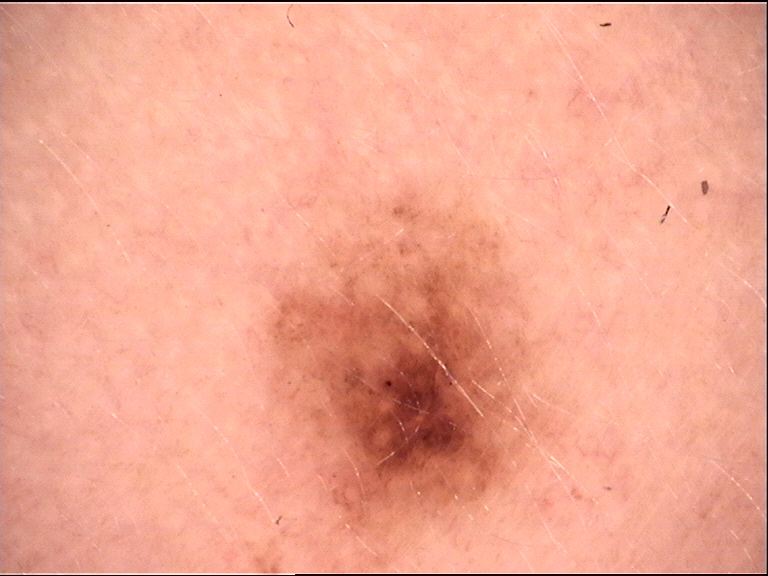Dermoscopy of a skin lesion. Consistent with a banal lesion — a compound nevus.